Dermoscopy of a skin lesion.
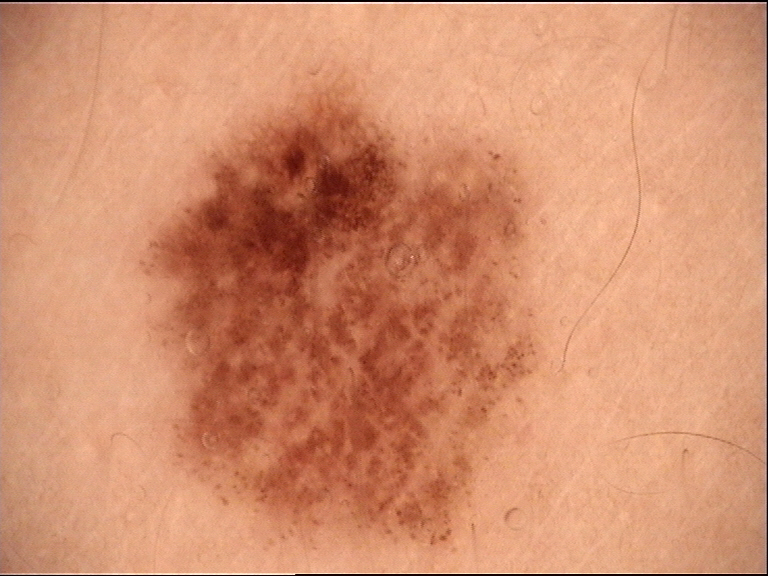Impression:
Diagnosed as a benign lesion — a dysplastic junctional nevus.